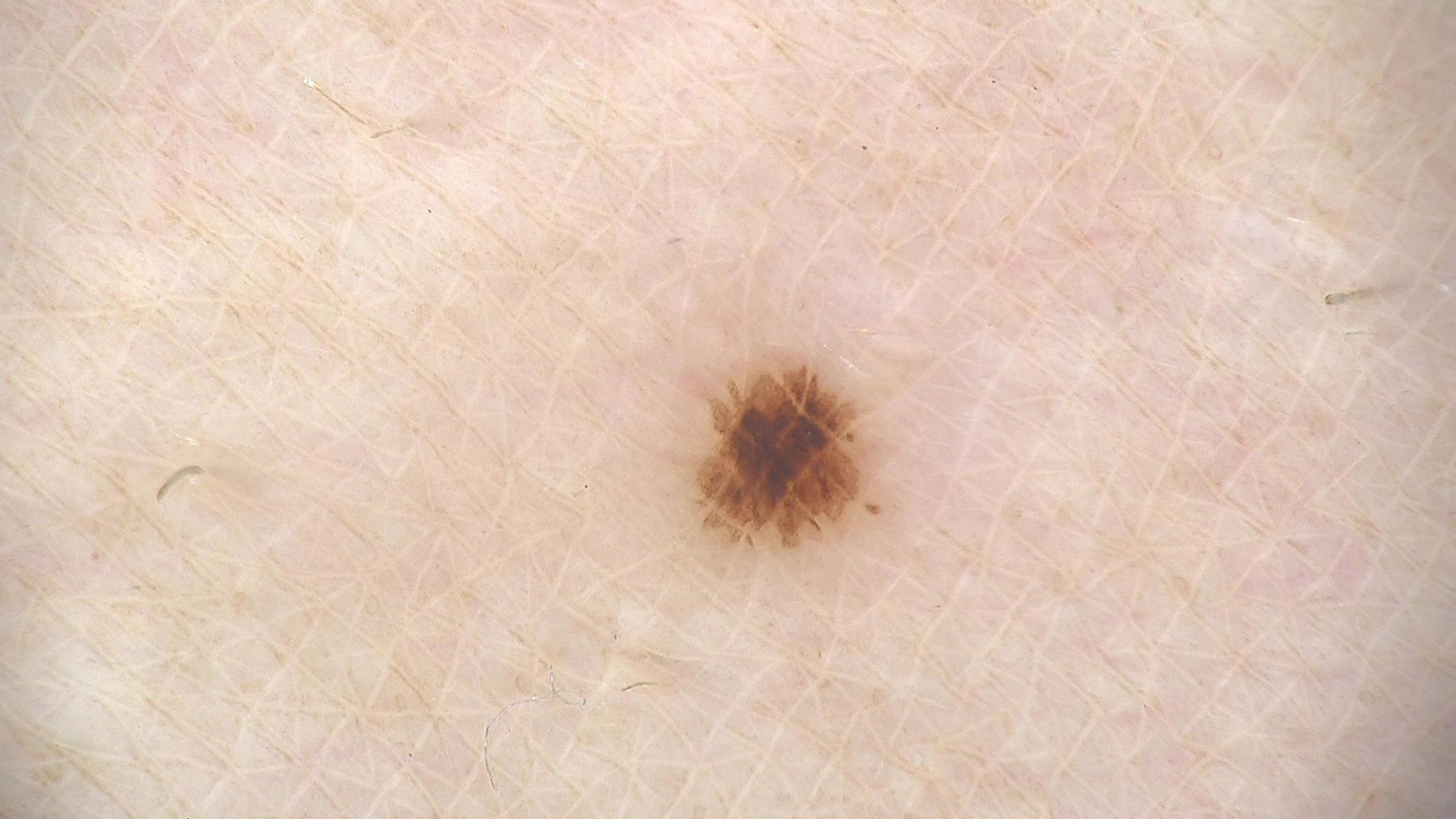Conclusion: Consistent with a benign lesion — a dysplastic junctional nevus.